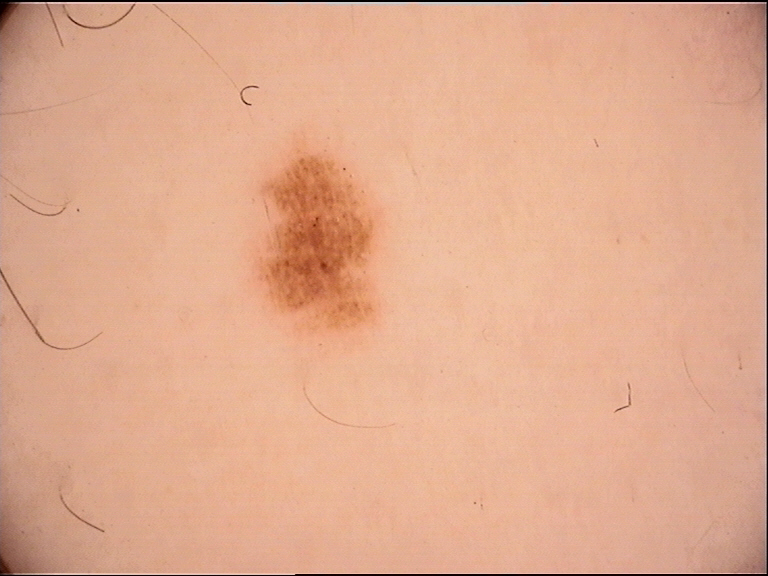Classified as a junctional nevus.